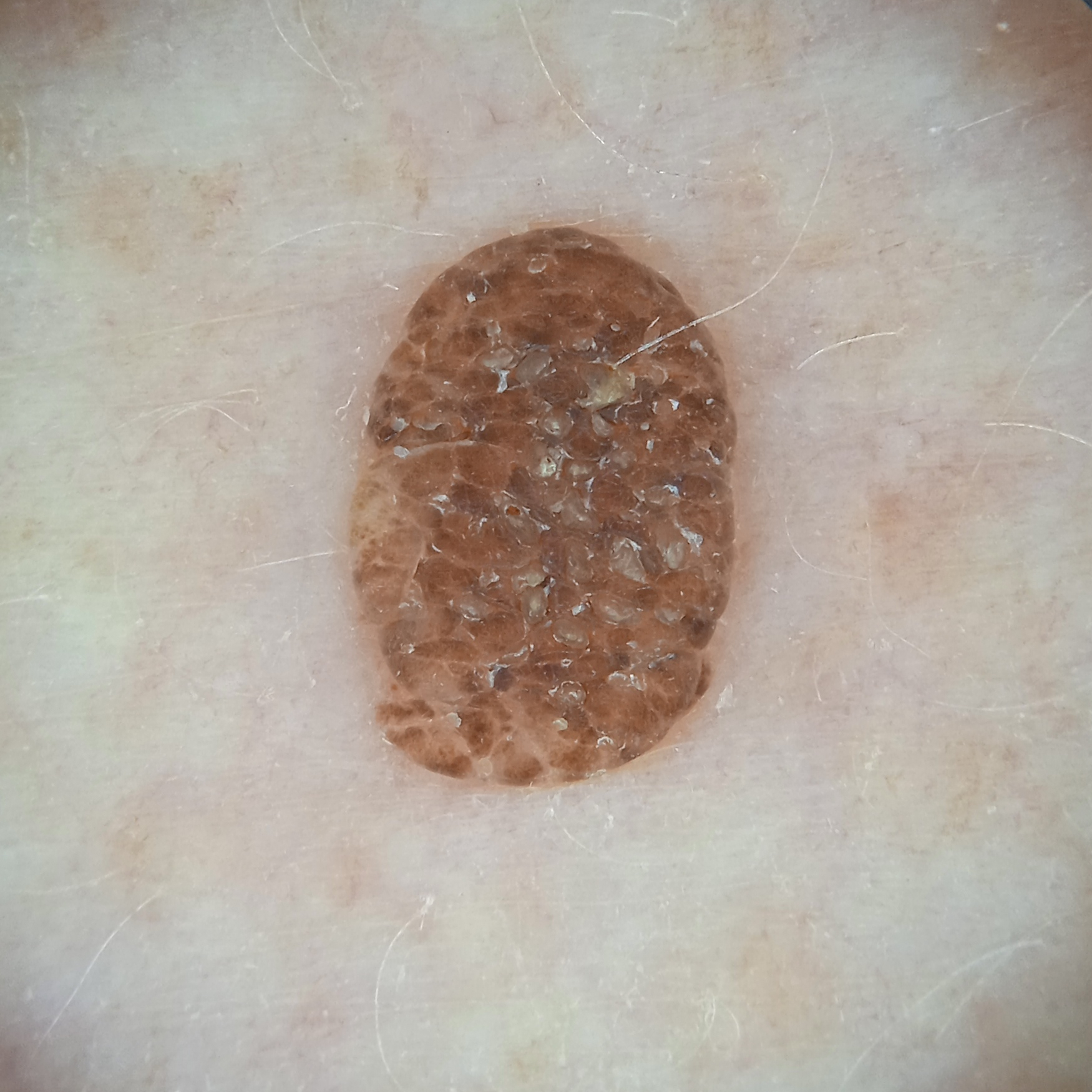Summary:
Dermoscopy of a skin lesion. Acquired for a research image collection, with no referral diagnosis. A female subject aged 78. The lesion is about 5.6 mm across.
Conclusion:
The four-dermatologist consensus diagnosis was a seborrheic keratosis; the reviewers' opinions were divided.